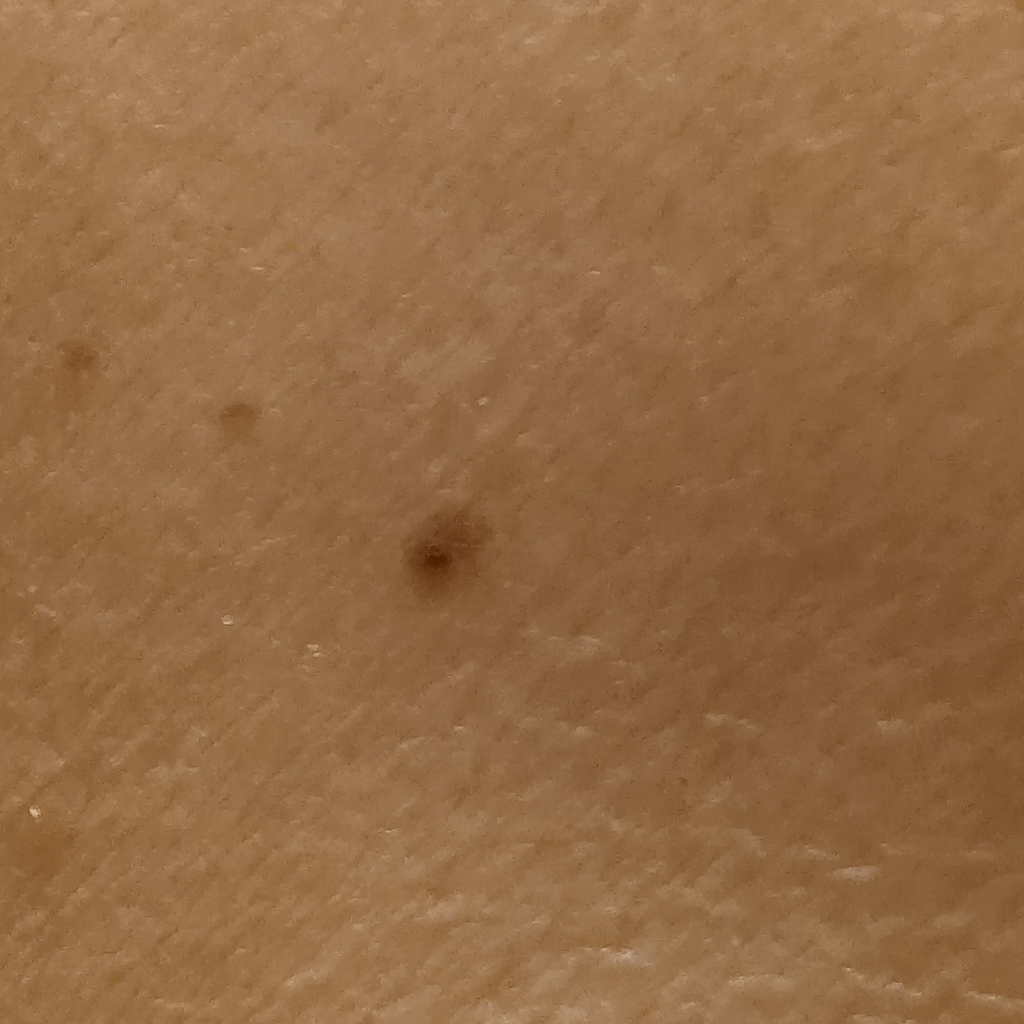| feature | finding |
|---|---|
| nevus count | a moderate number of melanocytic nevi |
| clinical context | research study (no referral diagnosis) |
| sun reaction | skin reddens painfully with sun exposure |
| subject | female, 81 years of age |
| assessment | melanocytic nevus (dermatologist consensus) |